A dermoscopic image of a skin lesion: 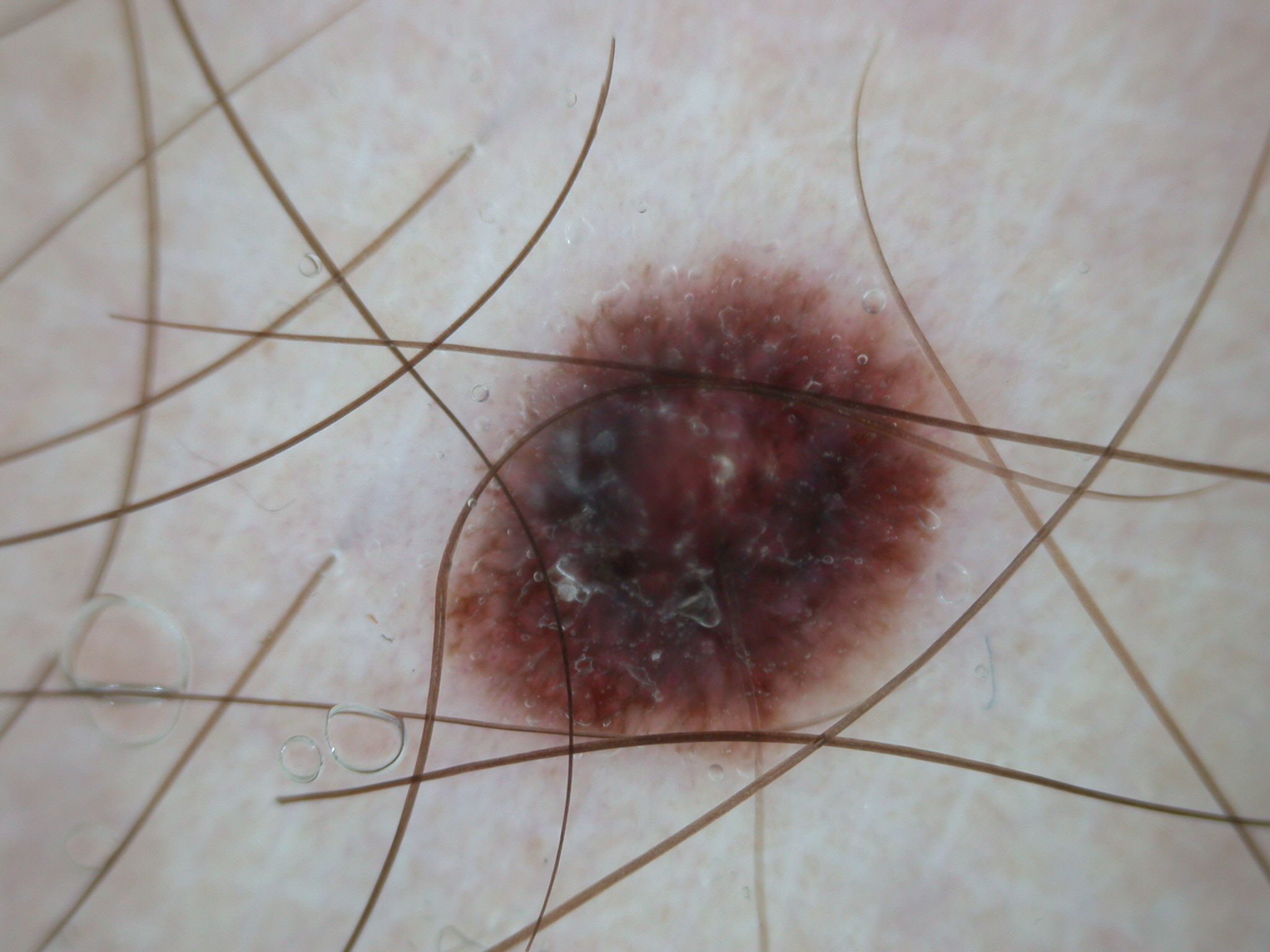lesion_extent: moderate
dermoscopic_features:
  present:
    - pigment network
    - streaks
  absent:
    - globules
    - negative network
    - milia-like cysts
lesion_location:
  bbox_xyxy:
    - 444
    - 255
    - 959
    - 759
diagnosis:
  name: melanocytic nevus
  malignancy: benign
  lineage: melanocytic
  provenance: clinical